A dermoscopy image of a single skin lesion.
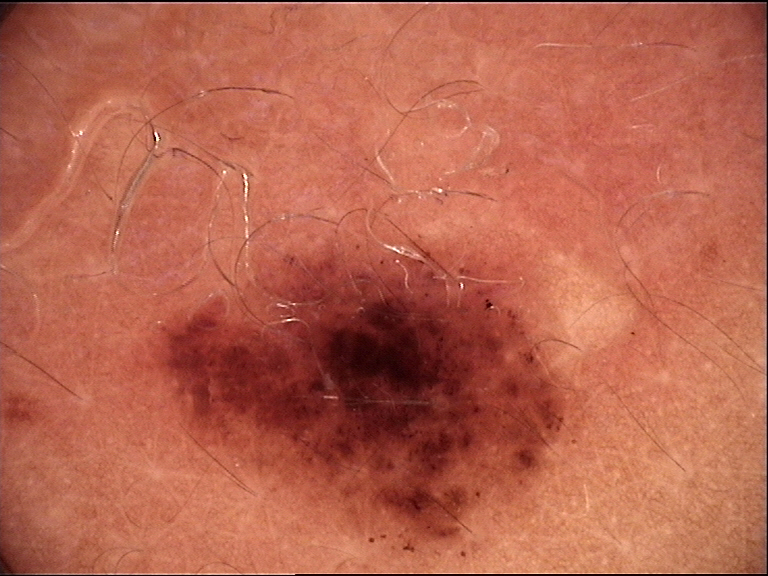The architecture is that of a banal lesion. Classified as a compound nevus.